The lesion is associated with itching · the patient reported no systemic symptoms · located on the arm · an image taken at a distance · present for three to twelve months · the patient considered this a rash:
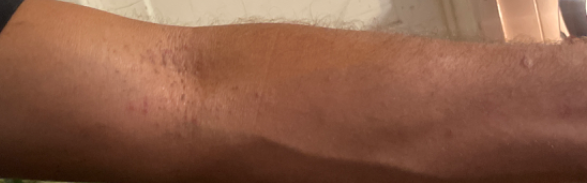Q: What was the assessment?
A: not assessable